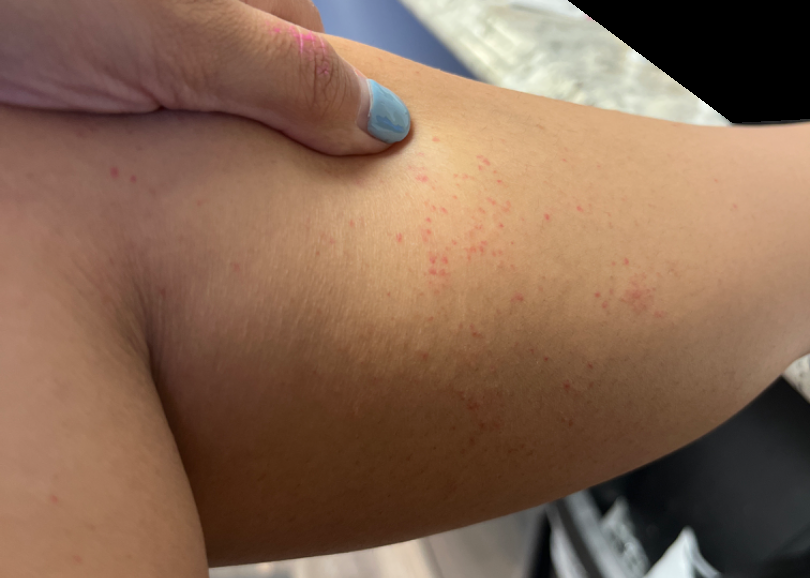Patient information:
This image was taken at an angle. Texture is reported as flat. Reported duration is about one day. The leg and arm are involved.
Review:
On remote review of the image: the differential includes Pigmented purpuric eruption, Eczema and Allergic Contact Dermatitis, with no clear leading consideration.